A dermoscopy image of a single skin lesion.
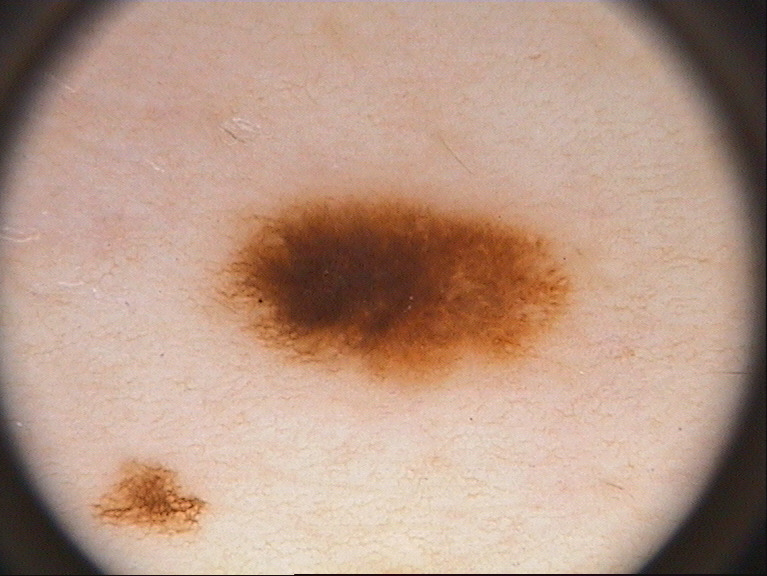Q: Which dermoscopic features were noted?
A: pigment network
Q: Lesion extent?
A: moderate
Q: Where is the lesion in the image?
A: bbox=[205, 192, 571, 392]
Q: What is this lesion?
A: a melanocytic nevus